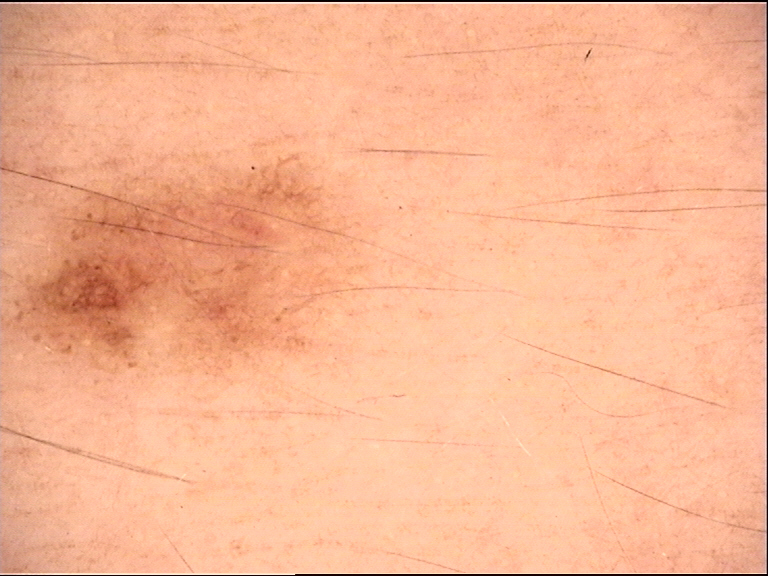A dermatoscopic image of a skin lesion.
The diagnosis was a benign lesion — a dysplastic junctional nevus.